The photograph was taken at an angle.
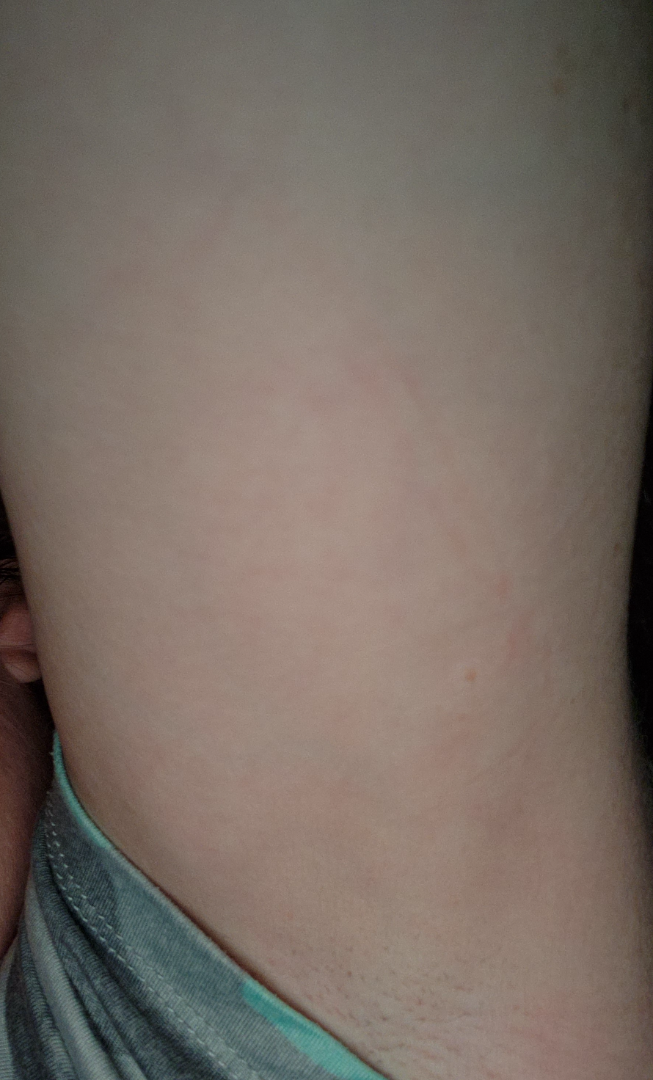  differential:
    tied_lead:
      - Allergic Contact Dermatitis
      - Irritant Contact Dermatitis